A dermoscopic image of a skin lesion.
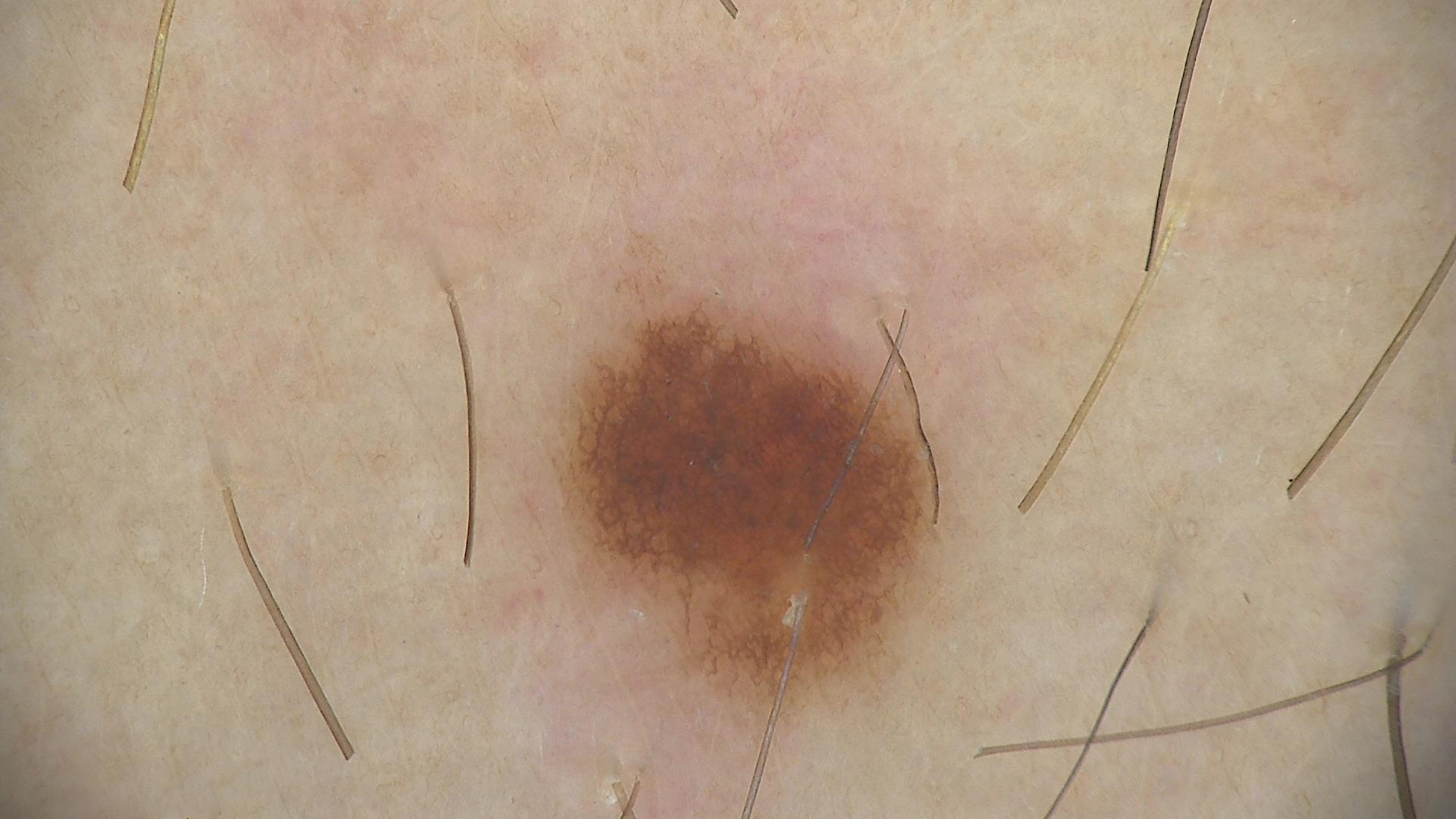The diagnosis was a dysplastic junctional nevus.